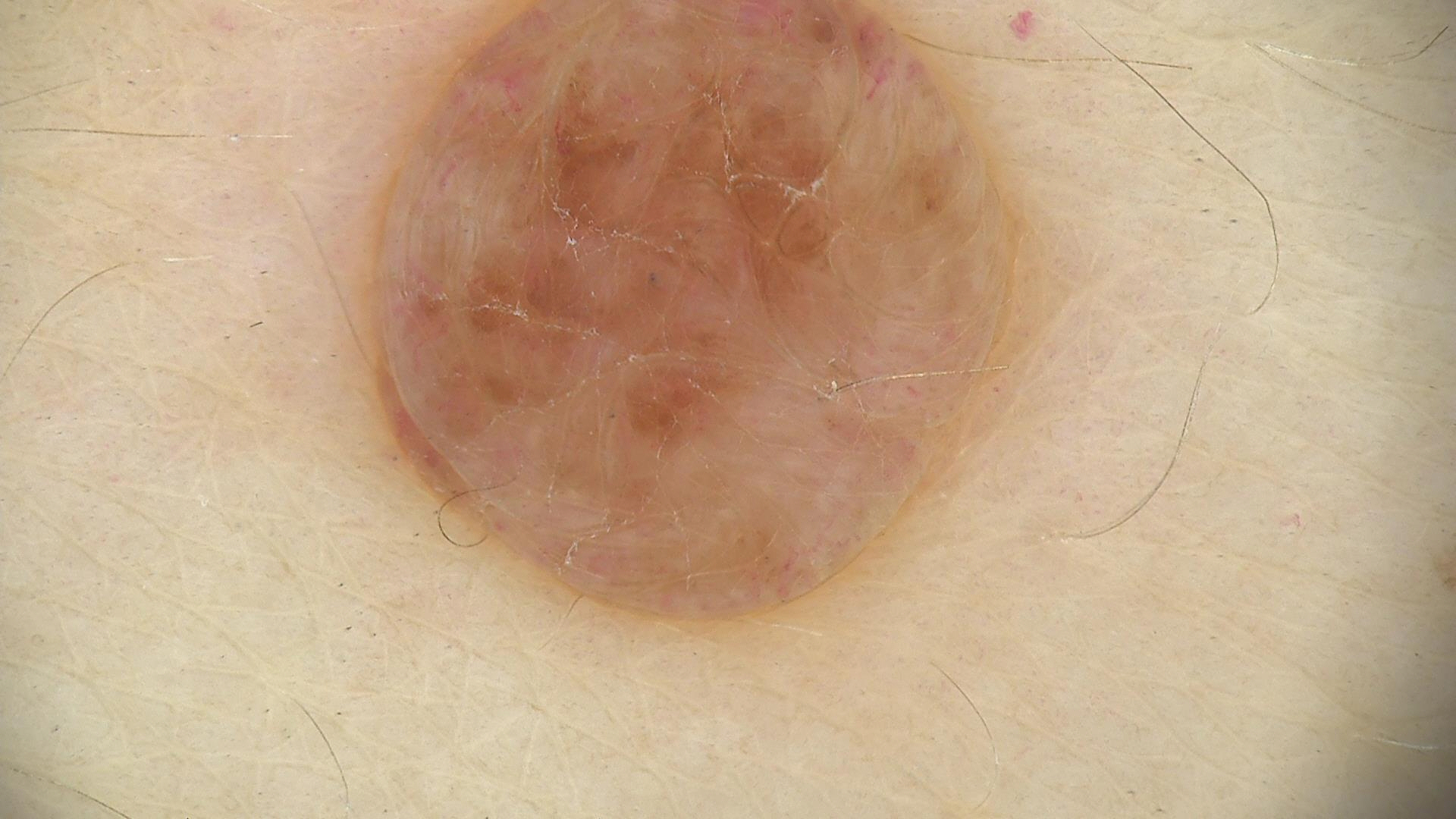<case>
  <image>dermoscopy</image>
  <lesion_type>
    <main_class>banal</main_class>
    <pattern>dermal</pattern>
  </lesion_type>
  <diagnosis>
    <name>dermal nevus</name>
    <code>db</code>
    <malignancy>benign</malignancy>
    <super_class>melanocytic</super_class>
    <confirmation>expert consensus</confirmation>
  </diagnosis>
</case>